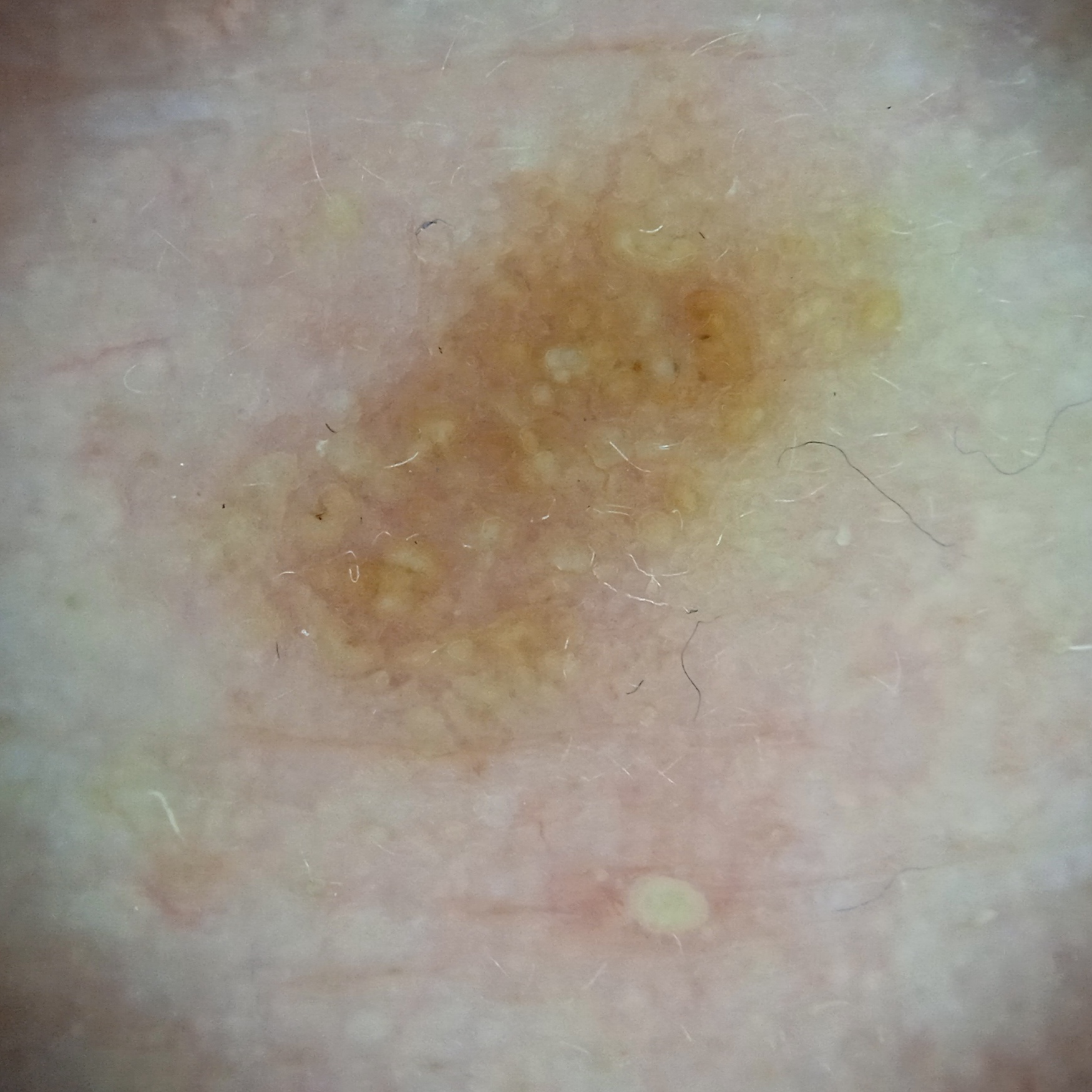  image: dermoscopy
  patient:
    age: 89
    sex: male
  referral: research study (no referral diagnosis)
  sun_reaction: skin reddens painfully with sun exposure
  lesion_location: the face
  lesion_size:
    diameter_mm: 6.4
  diagnosis:
    name: actinic keratosis
    malignancy: benign
    certainty: good